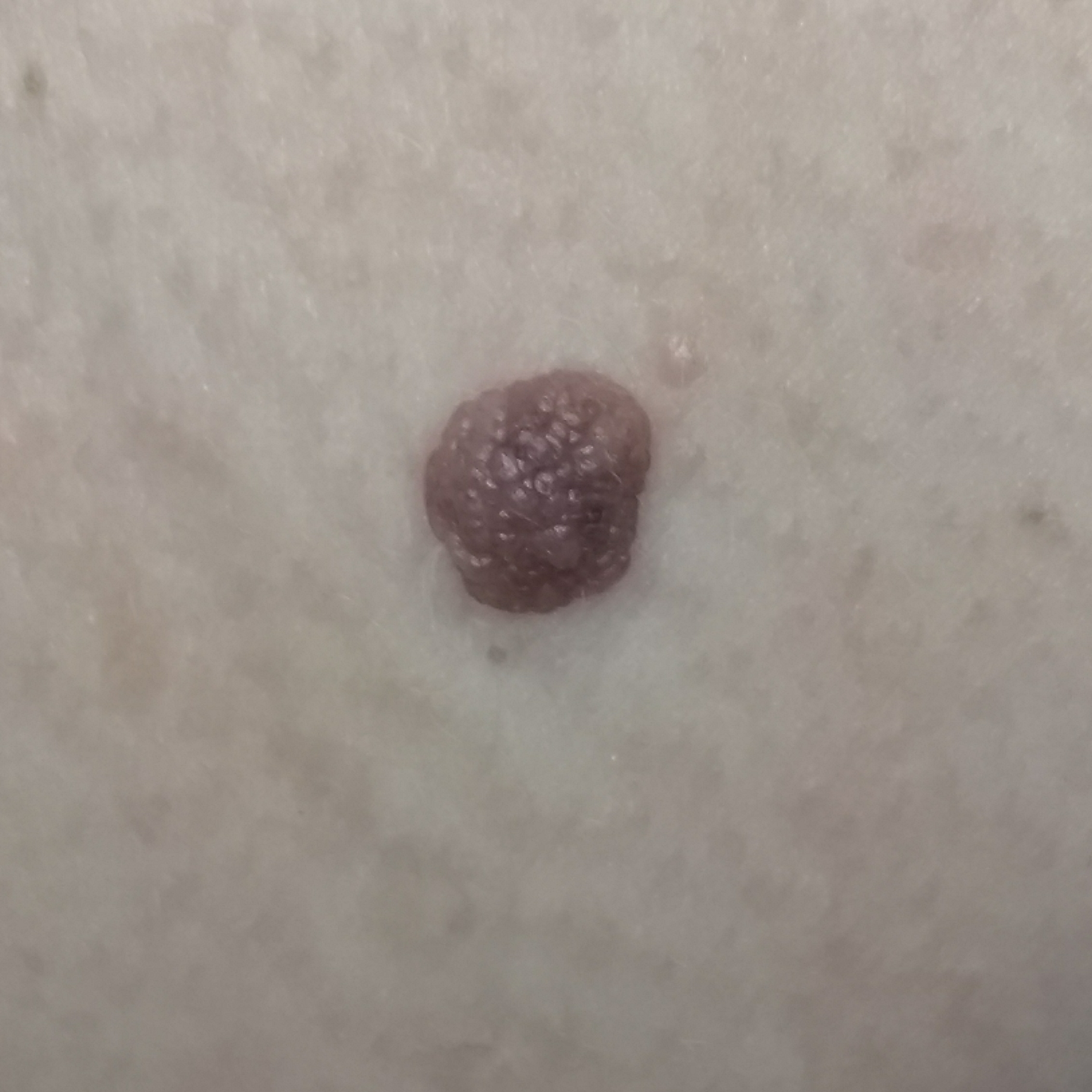| field | value |
|---|---|
| patient | age 39 |
| anatomic site | the neck |
| symptoms | growth, elevation / no itching, no pain |
| impression | nevus (clinical consensus) |